A female subject 75 years old · a clinical photo of a skin lesion taken with a smartphone:
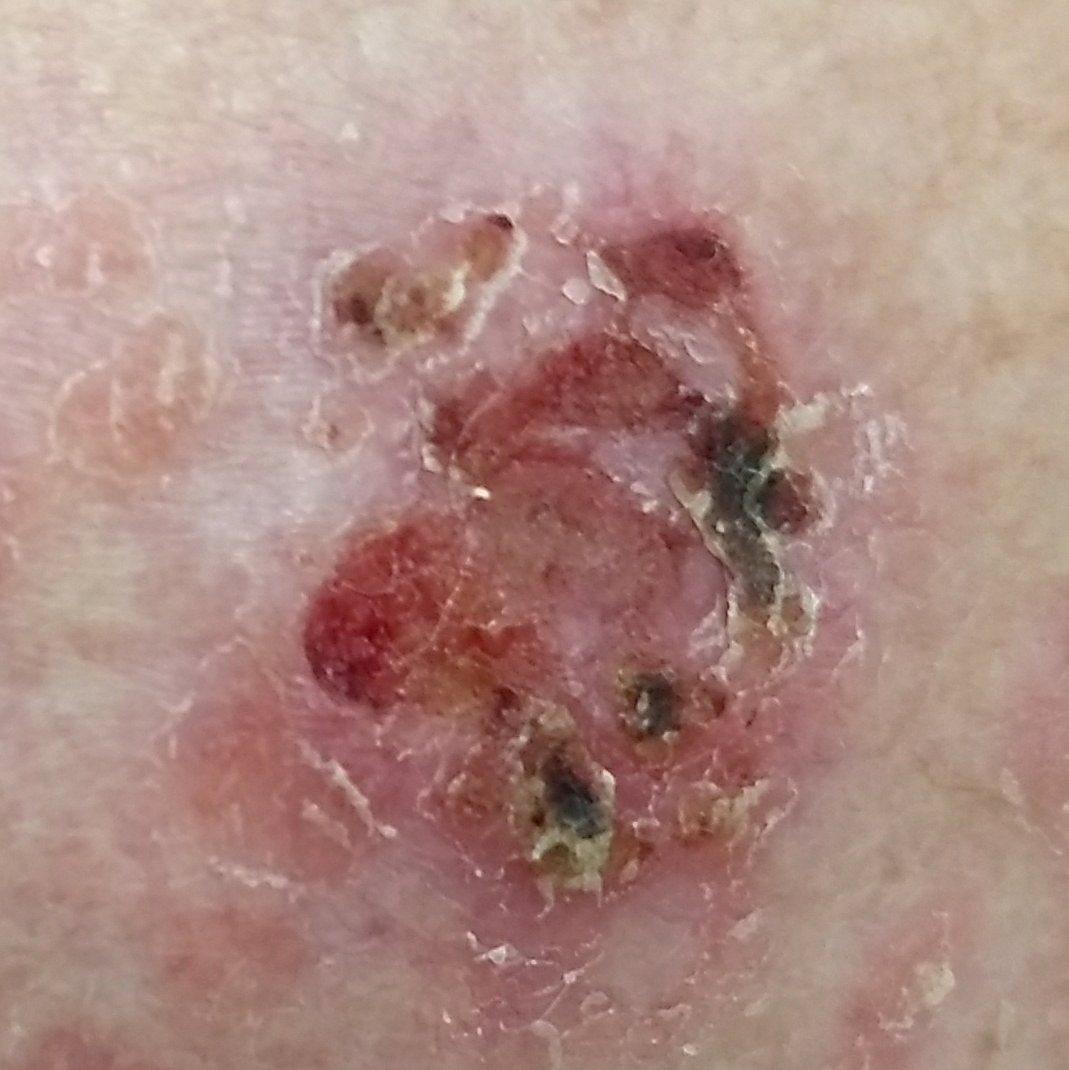location: the chest
patient-reported symptoms: itching, elevation, bleeding, pain
diagnosis: basal cell carcinoma (biopsy-proven)